A moderate number of moles by the patient's own estimate; a dermoscopy image of a skin lesion; the patient says their skin tans without first burning.
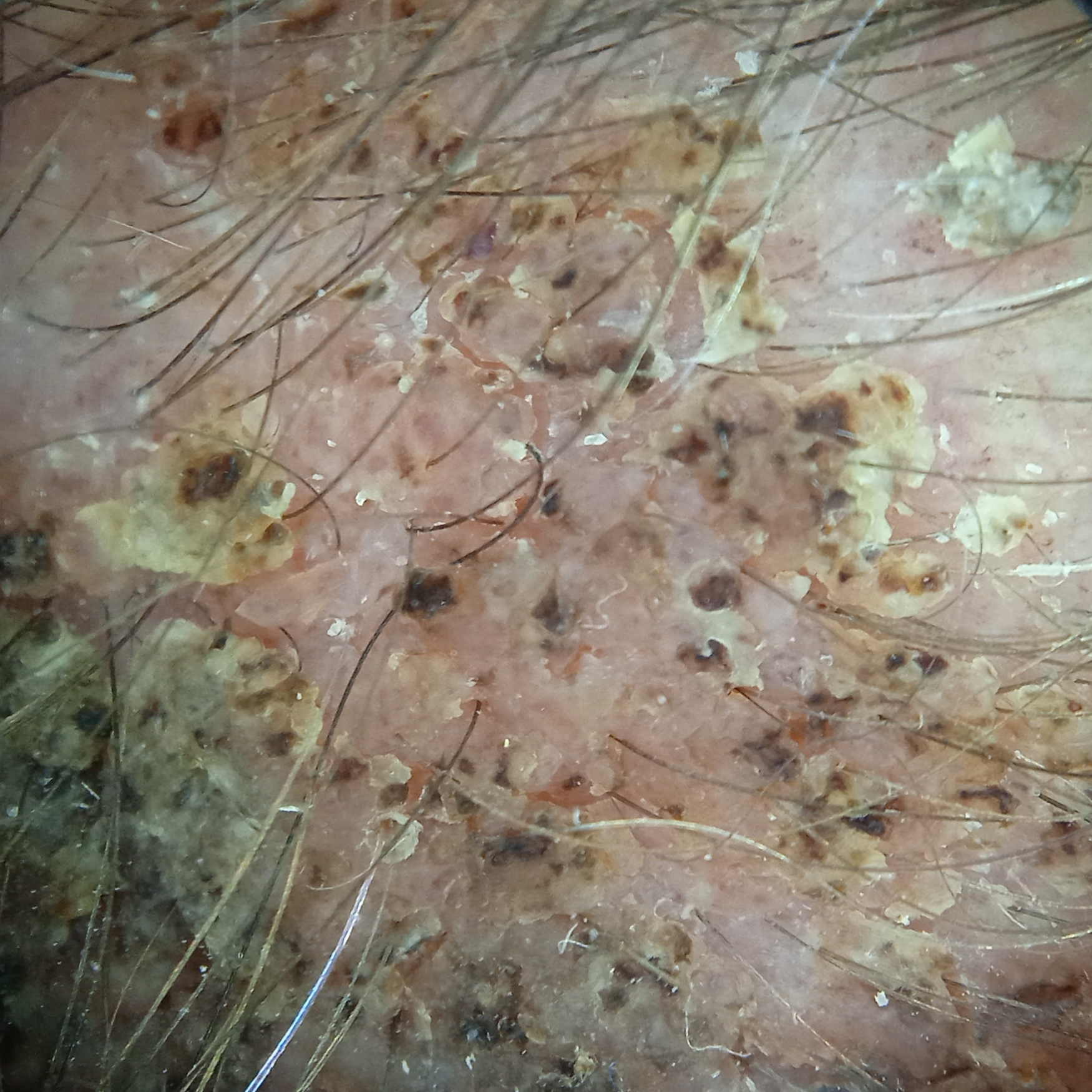The lesion involves the head. Measuring roughly 19.2 mm. The lesion was assessed as a seborrheic keratosis.